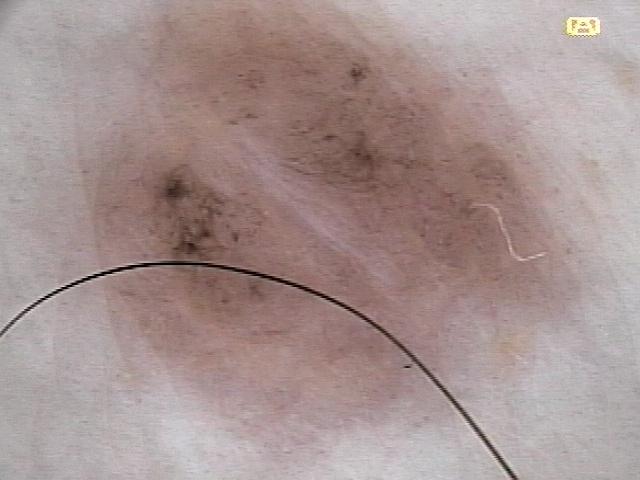The chart notes no first-degree relative with melanoma and no prior melanoma. A female subject roughly 65 years of age. The lesion is located on a lower extremity. Confirmed on histopathology as a benign, melanocytic lesion — a nevus.